Located on the arm; this image was taken at a distance:
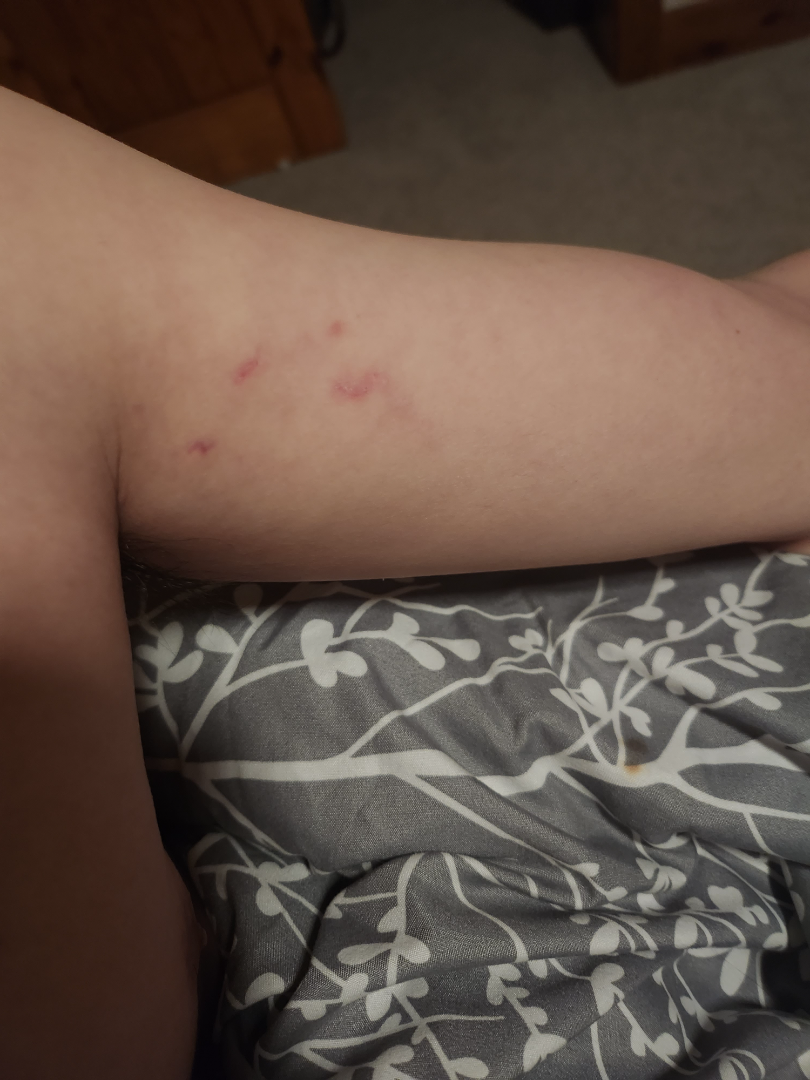diagnostic considerations = Abrasion, scrape, or scab; Skin striae; and Animal bite - wound were considered with similar weight.